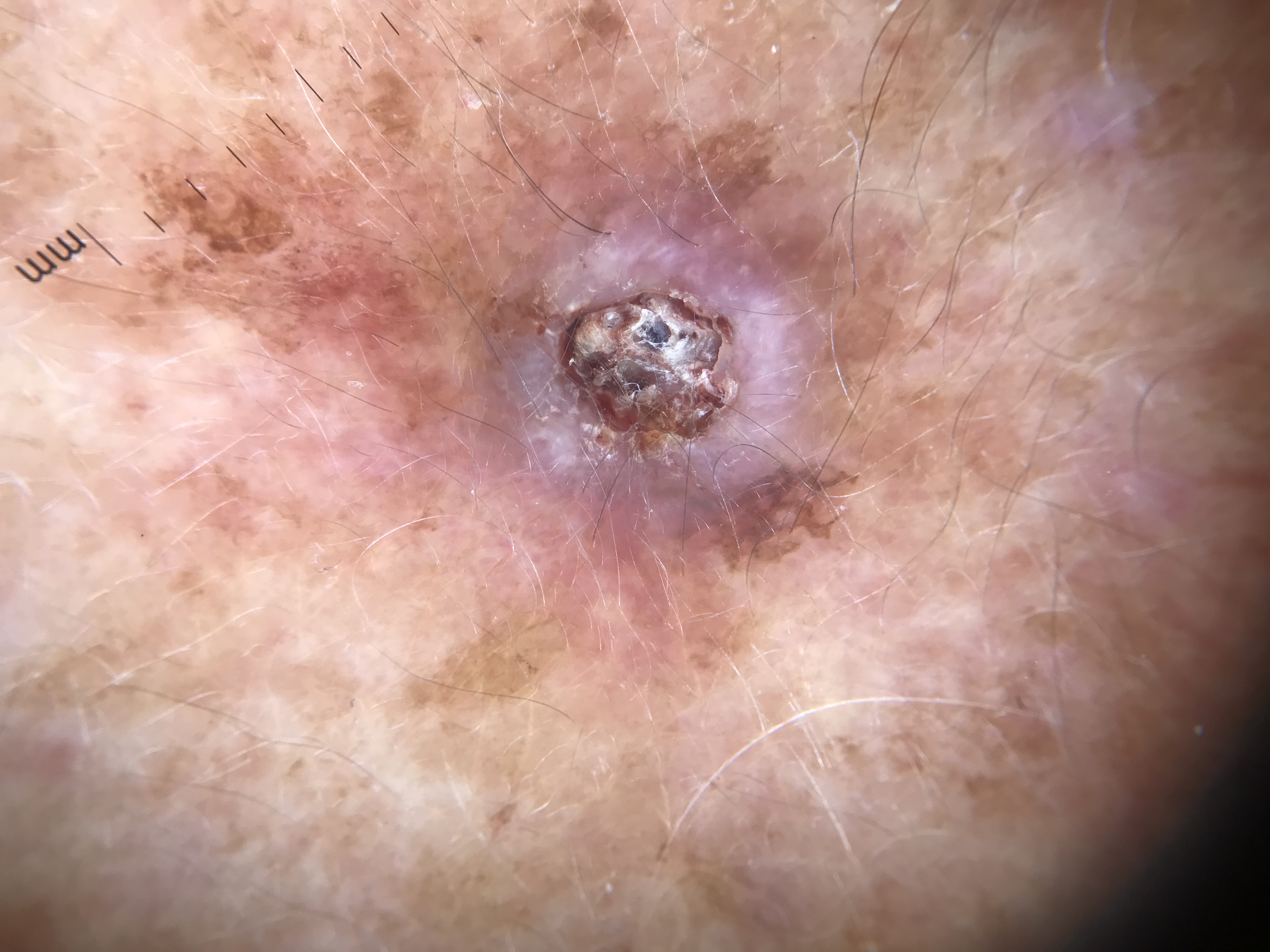Dermoscopy of a skin lesion.
The morphology is that of a keratinocytic lesion.
Histopathology confirmed a skin cancer — a squamous cell carcinoma.